The lesion involves the head or neck, leg and top or side of the foot · present for one to three months · associated systemic symptoms include joint pain and fatigue · an image taken at an angle — 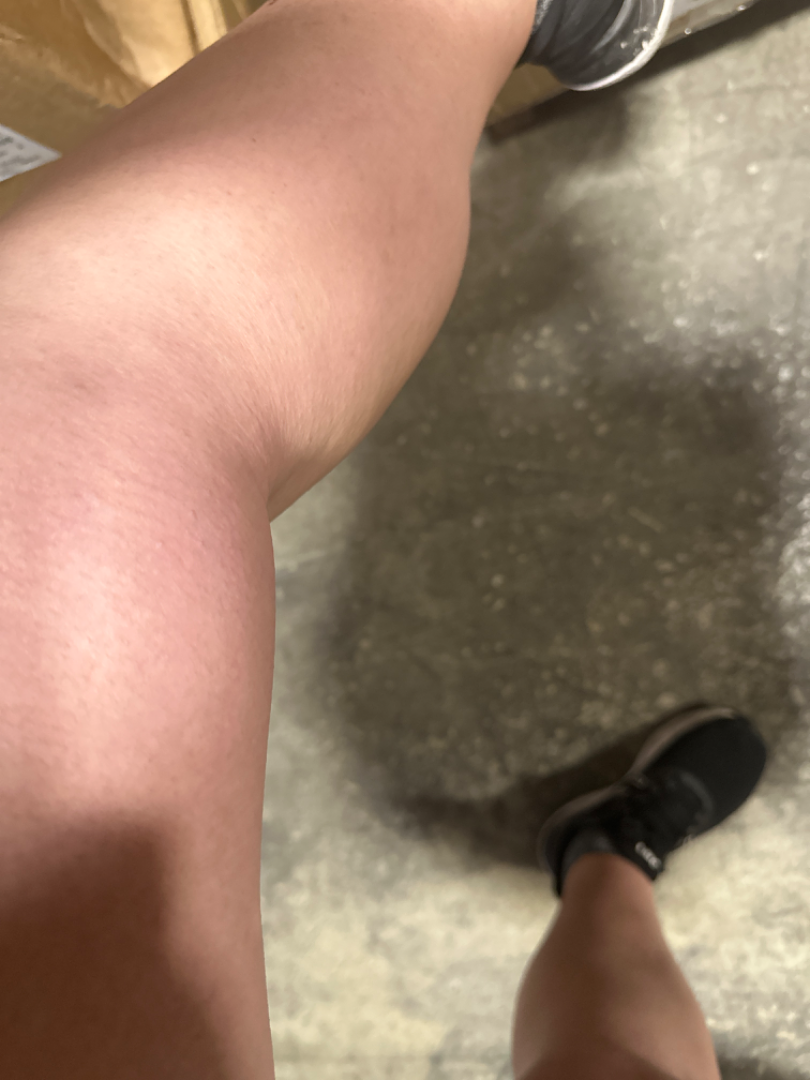<dermatology_case>
<assessment>ungradable on photographic review</assessment>
</dermatology_case>